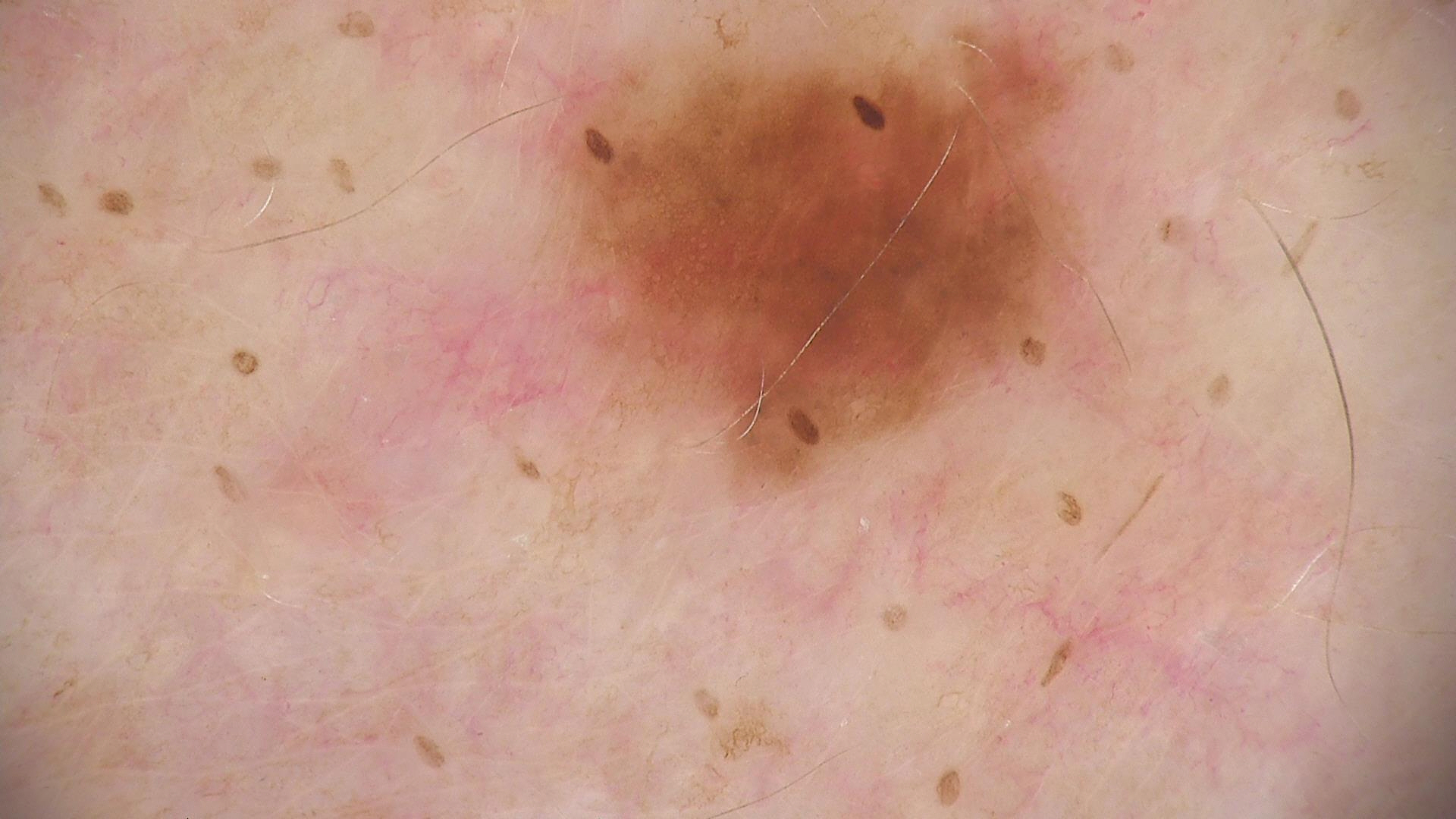Findings:
– image type: dermatoscopy
– class: dysplastic junctional nevus (expert consensus)